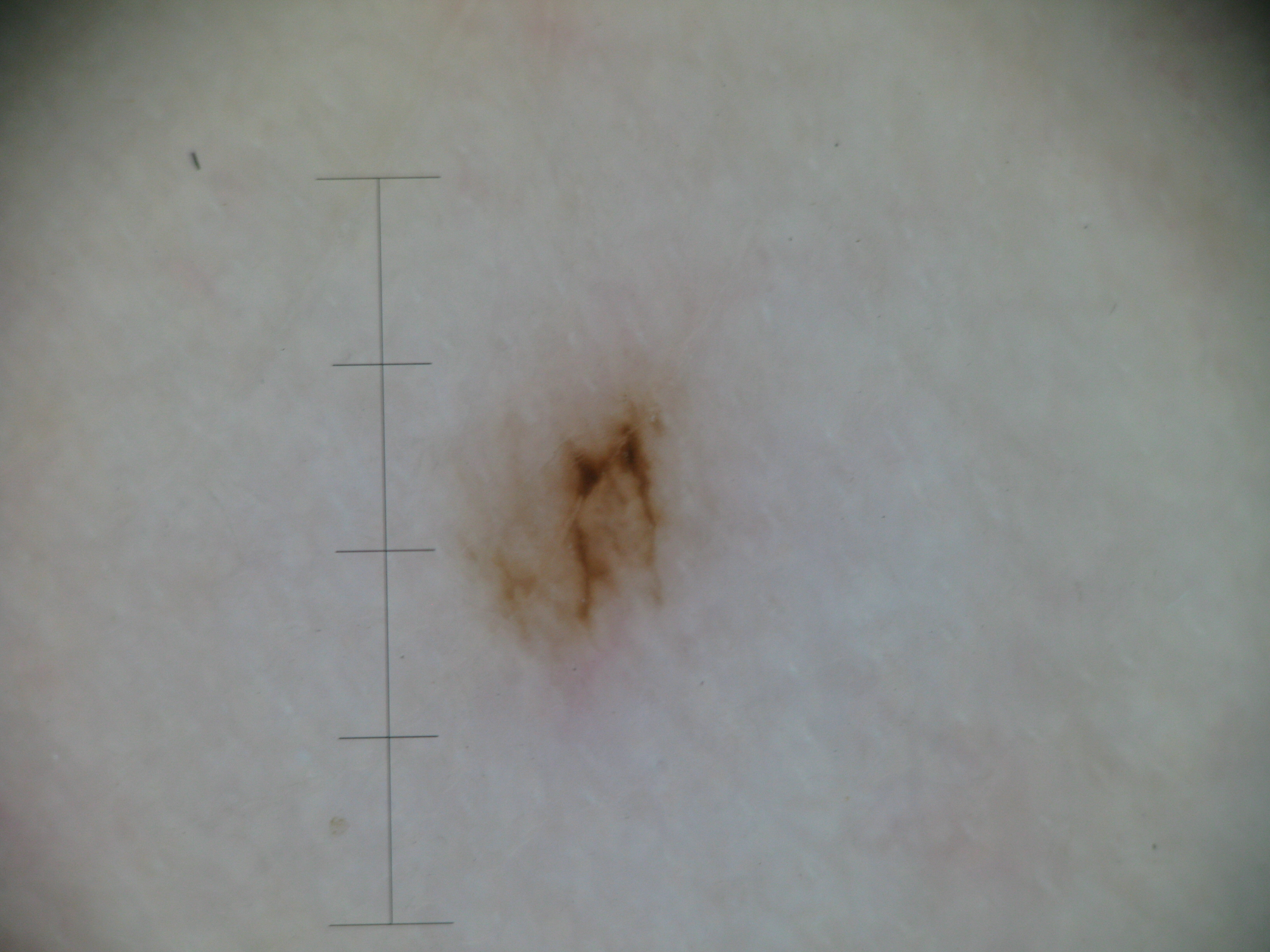A dermoscopy image of a single skin lesion.
The diagnosis was a benign lesion — an acral dysplastic junctional nevus.